This image was taken at a distance — 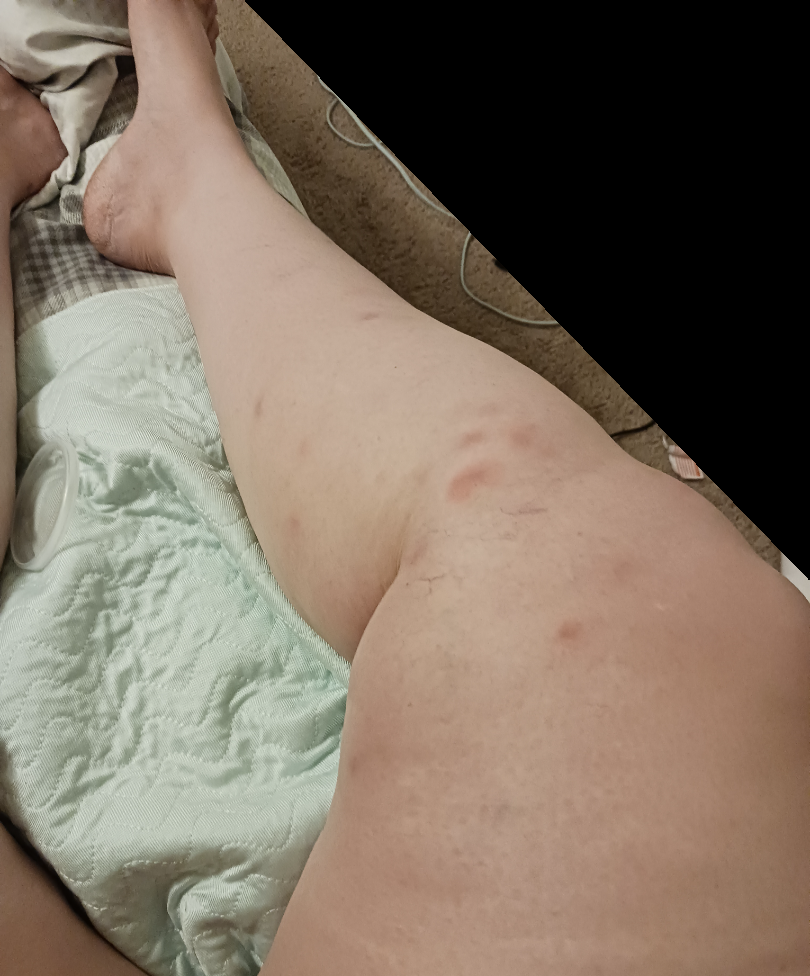Assessment:
The reviewing clinician's impression was: the favored diagnosis is Erythema nodosum.